The patient is male; the lesion involves the front of the torso; close-up view.
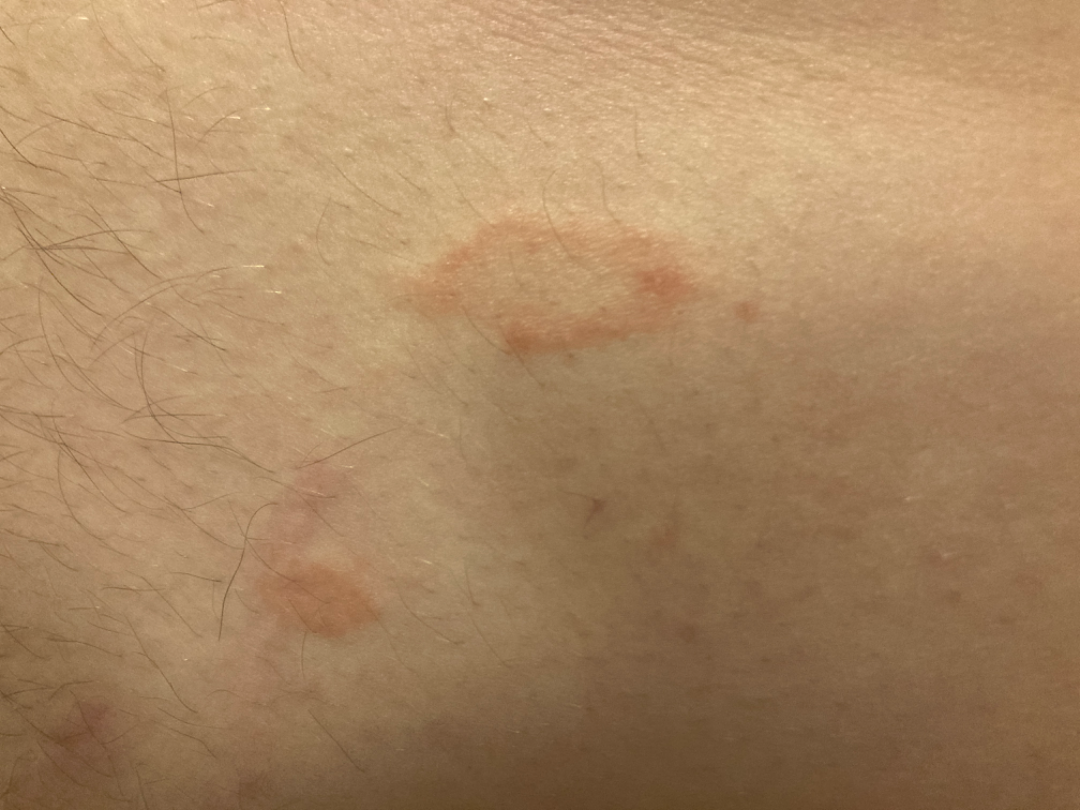Clinical context:
The patient notes itching. Present for one to four weeks. Skin tone: Fitzpatrick I; non-clinician graders estimated MST 4 (US pool) or 3 (India pool). The lesion is described as raised or bumpy and rough or flaky. Self-categorized by the patient as a rash.
Assessment:
Pityriasis rosea (55%); Tinea (25%); Psoriasis (11%); Eczema (9%).